This image was taken at an angle; the patient is 40–49, female; the lesion involves the leg, arm and head or neck.
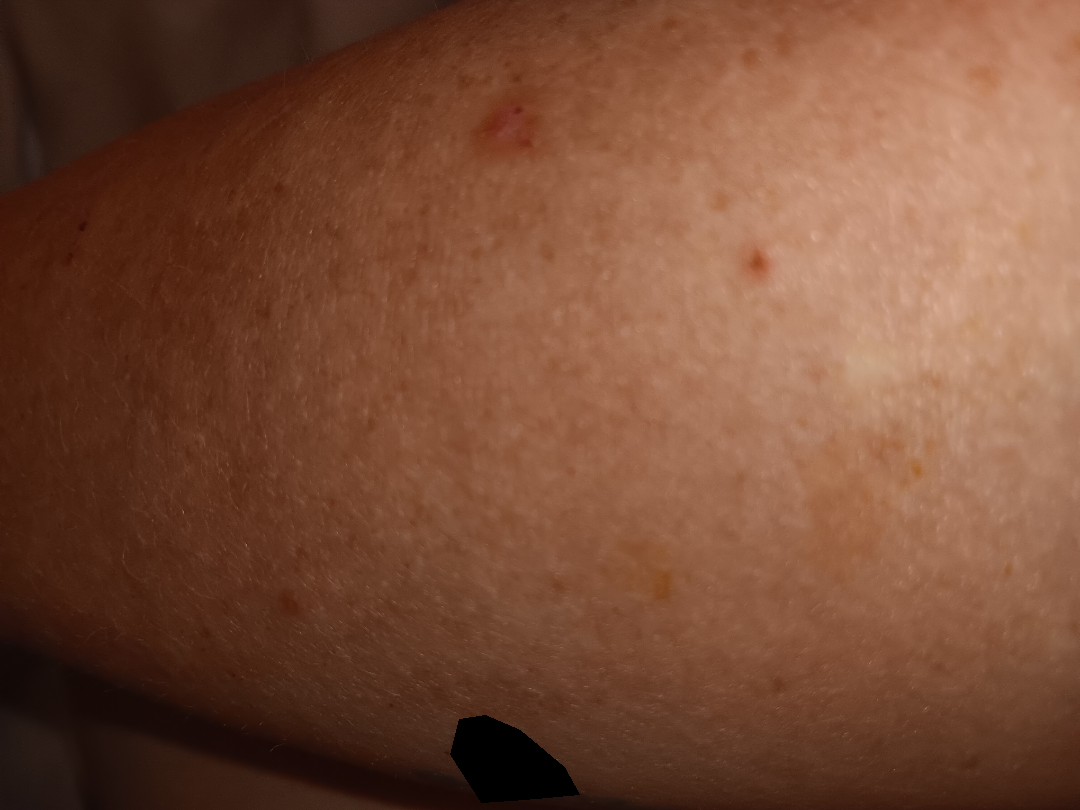The favored diagnosis is Actinic Keratosis; an alternative is Herpes Zoster; the differential also includes Eczema; a remote consideration is Inflicted skin lesions; less likely is SCC/SCCIS.